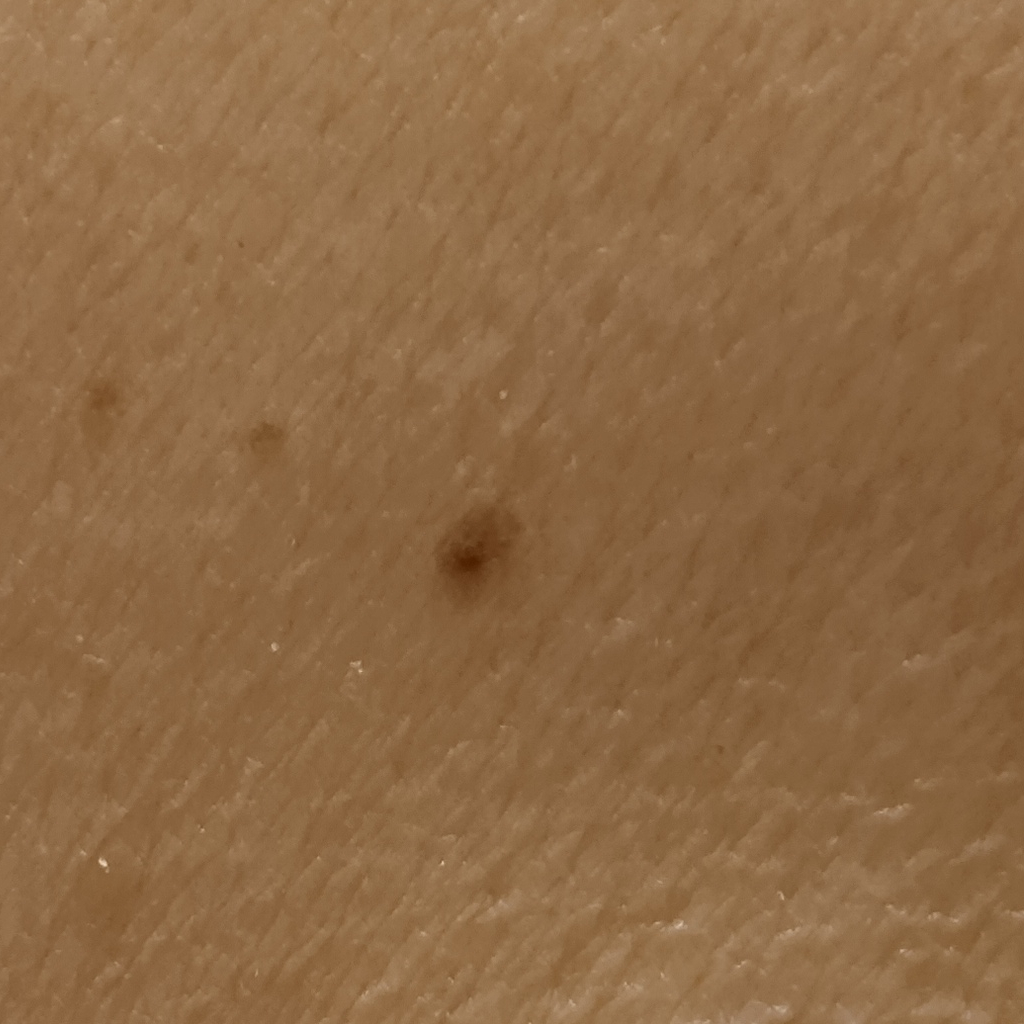A macroscopic clinical photograph of a skin lesion.
The patient describes having a moderate number of moles.
The lesion involves the back.
The lesion is about 2.7 mm across.
The lesion was assessed as a melanocytic nevus.